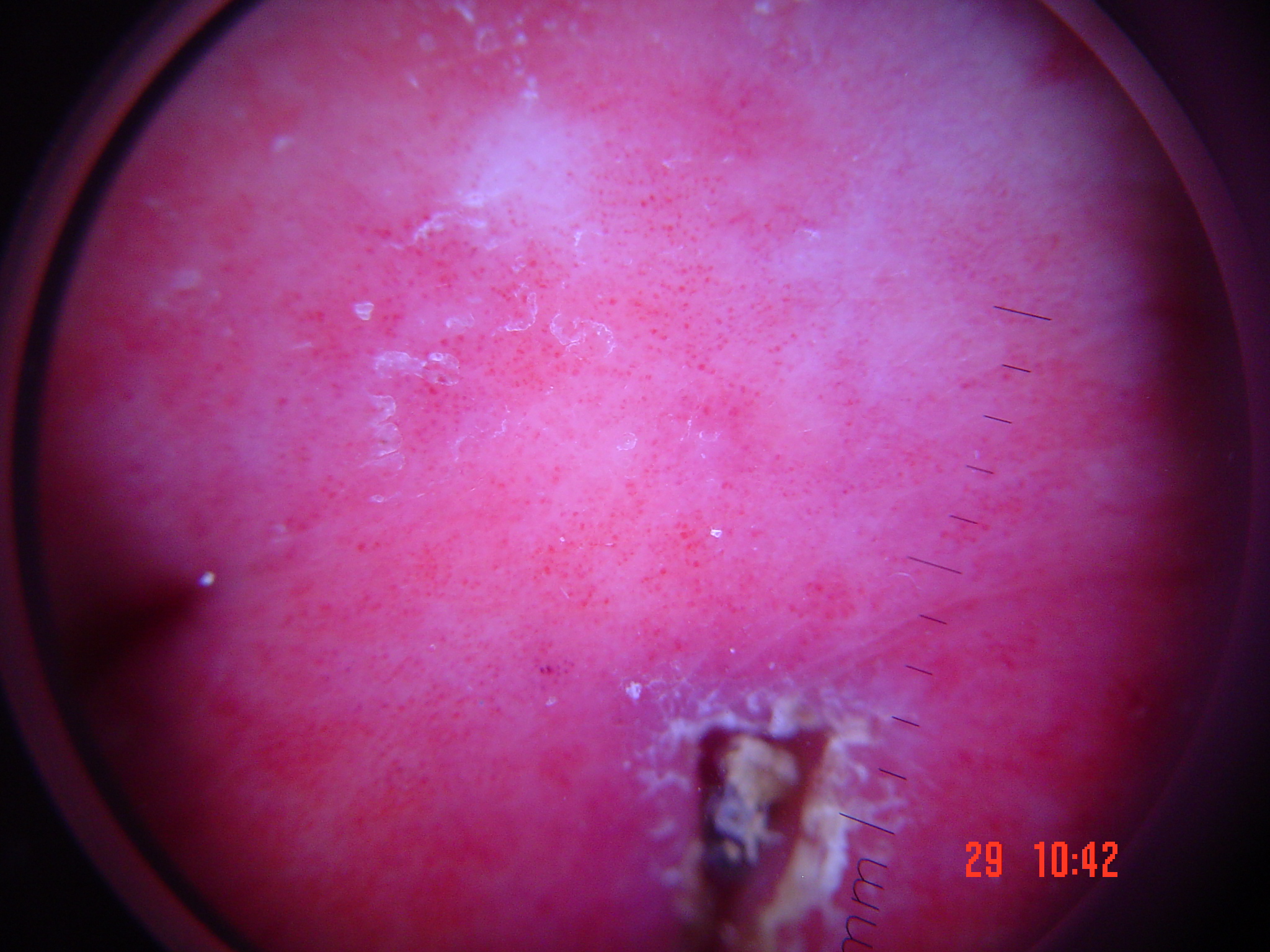lesion type=vascular | diagnosis=hemangioma (expert consensus).